No associated systemic symptoms reported · the patient reported no relevant symptoms from the lesion · the photograph is a close-up of the affected area · the lesion is described as rough or flaky and flat · self-categorized by the patient as a rash · present for less than one week · the affected area is the front of the torso.
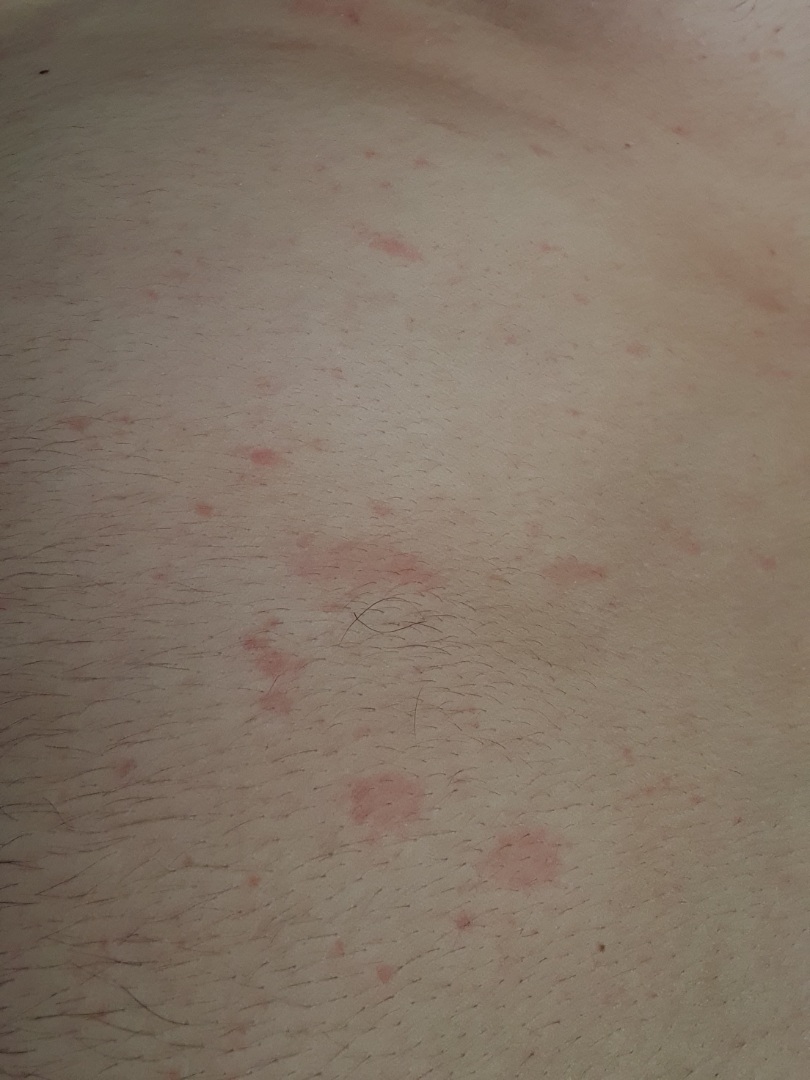Review:
The skin findings could not be characterized from the image.